A dermatoscopic image of a skin lesion.
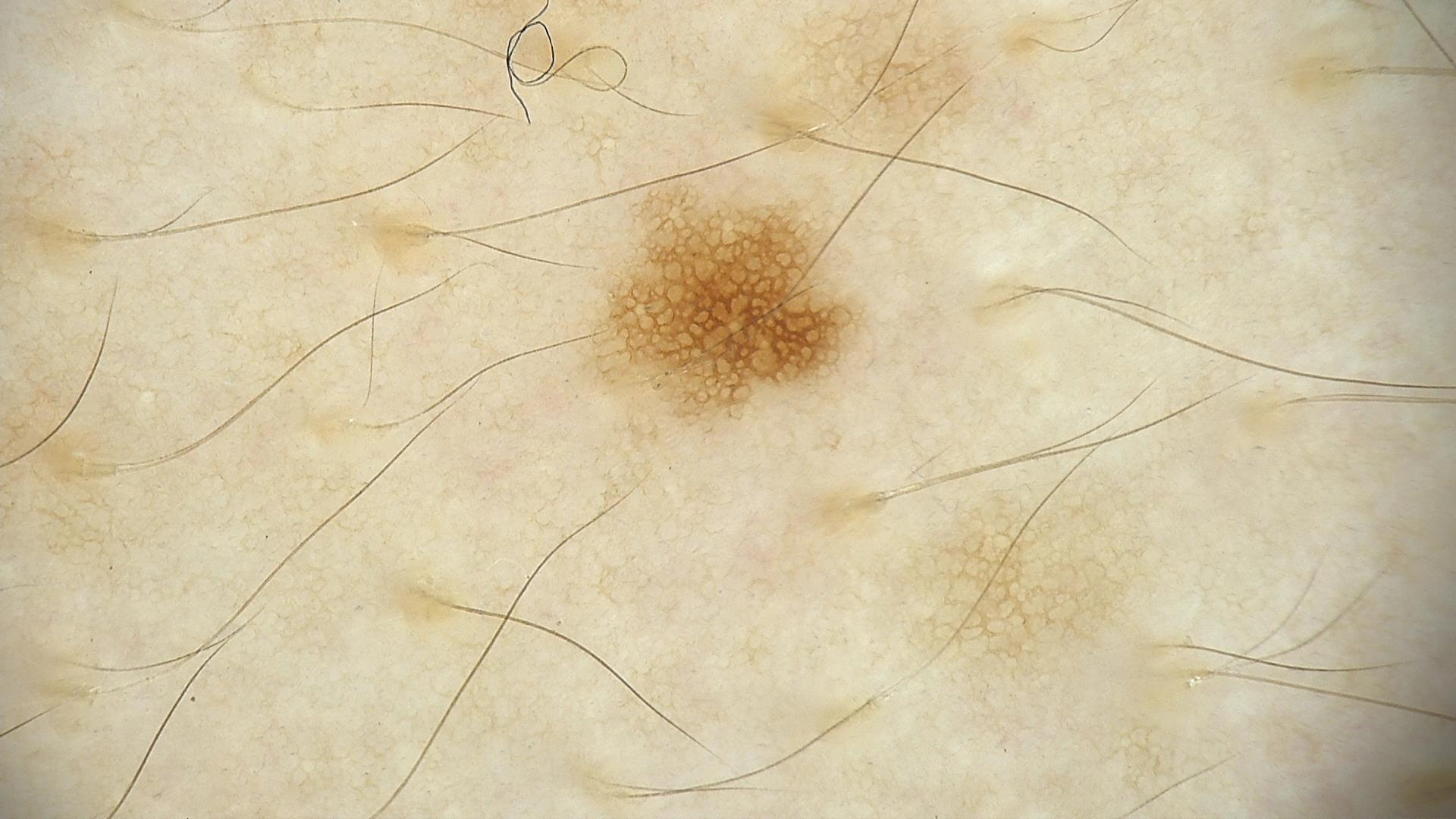Q: What was the diagnostic impression?
A: dysplastic junctional nevus (expert consensus)